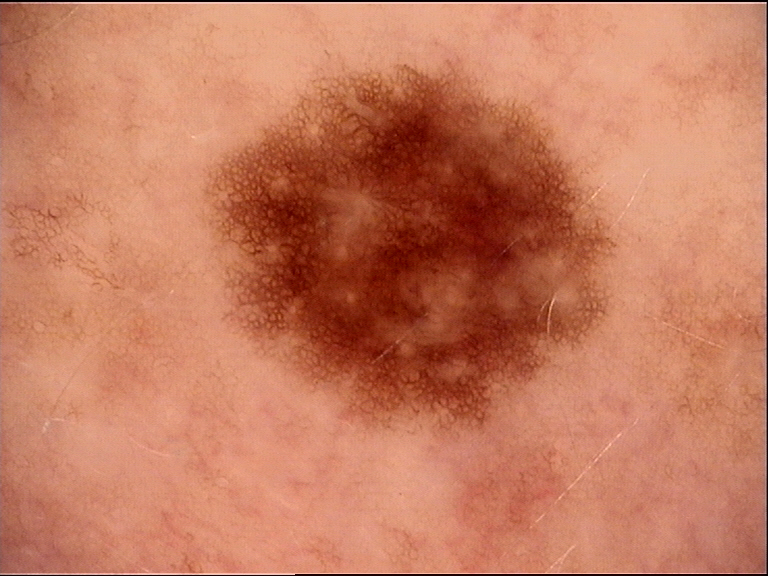A dermatoscopic image of a skin lesion. Consistent with a dysplastic junctional nevus.